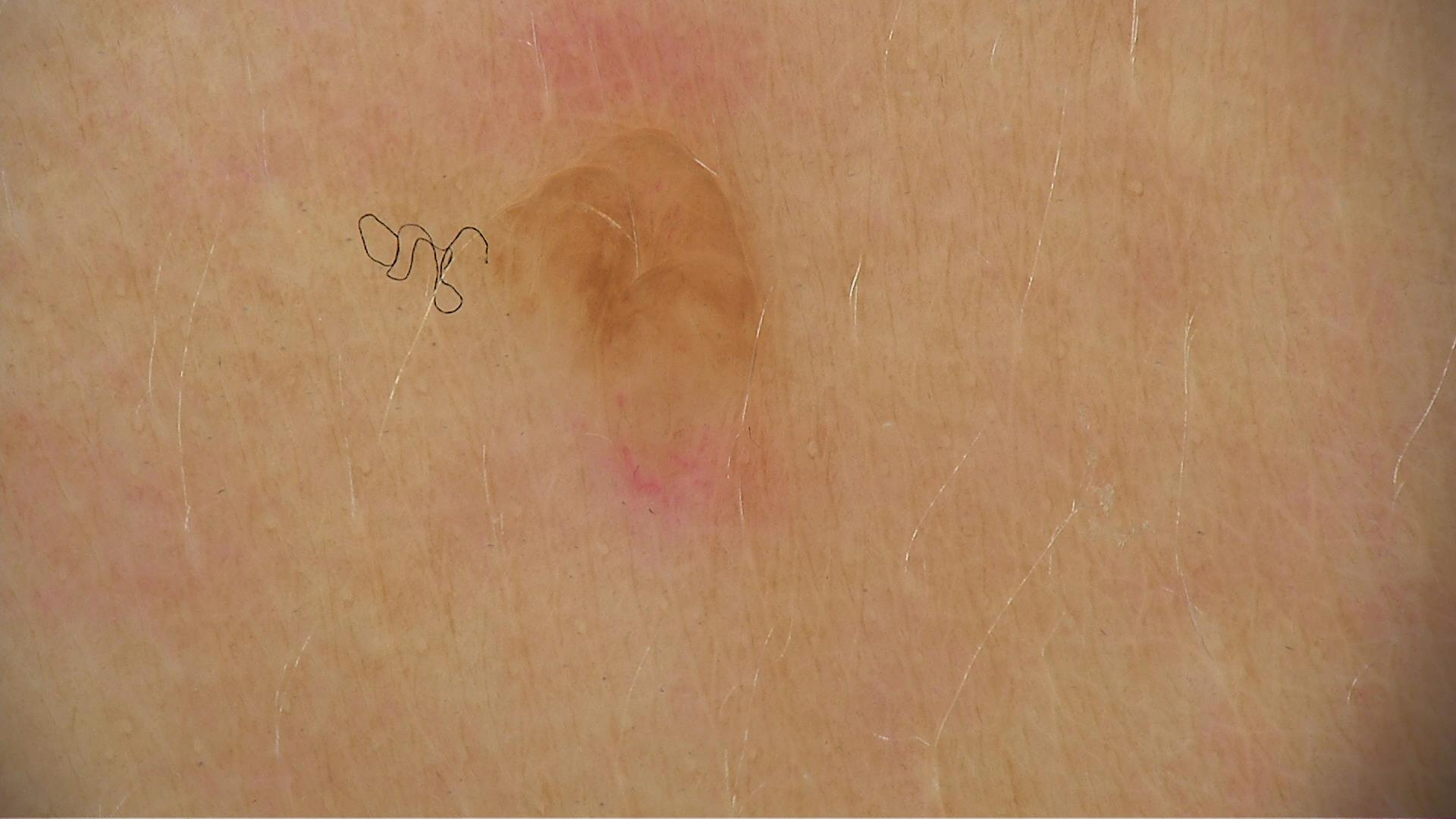Findings:
• classification · banal
• class · dermal nevus (expert consensus)